A dermatoscopic image of a skin lesion: 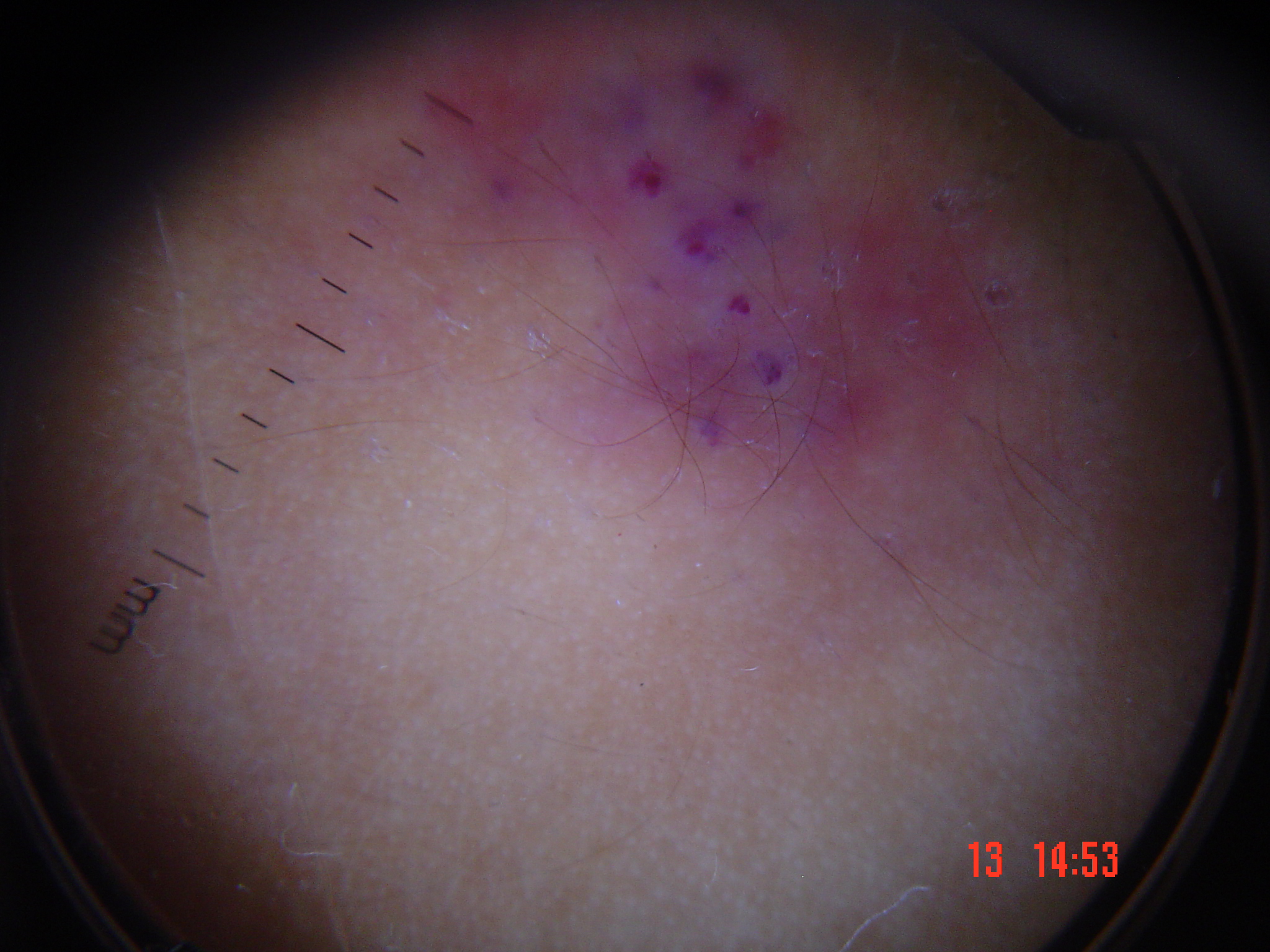category = vascular
assessment = angiokeratoma (expert consensus)